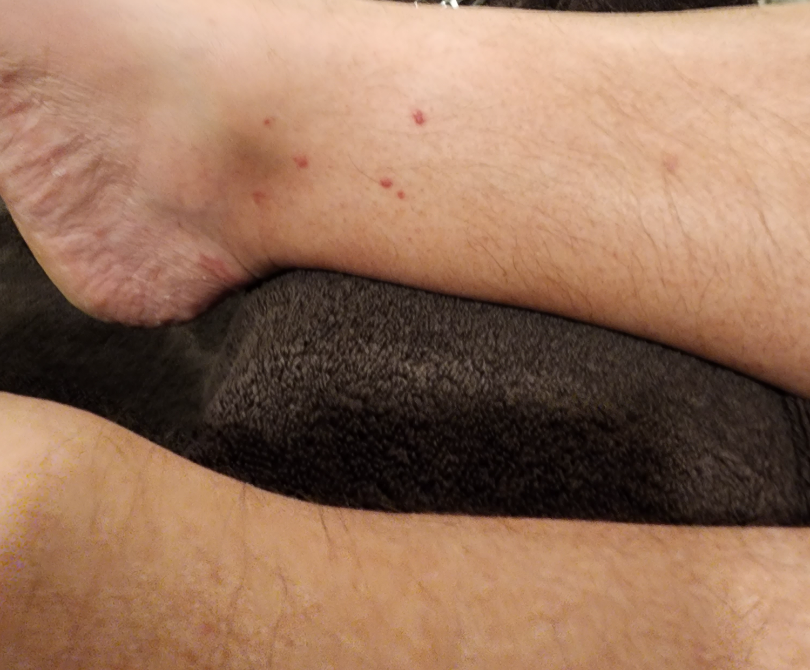History: The lesion involves the leg and top or side of the foot. An image taken at an angle. Impression: Pigmented purpuric eruption (possible); Leukocytoclastic Vasculitis (possible); Kaposi's sarcoma of skin (less likely).